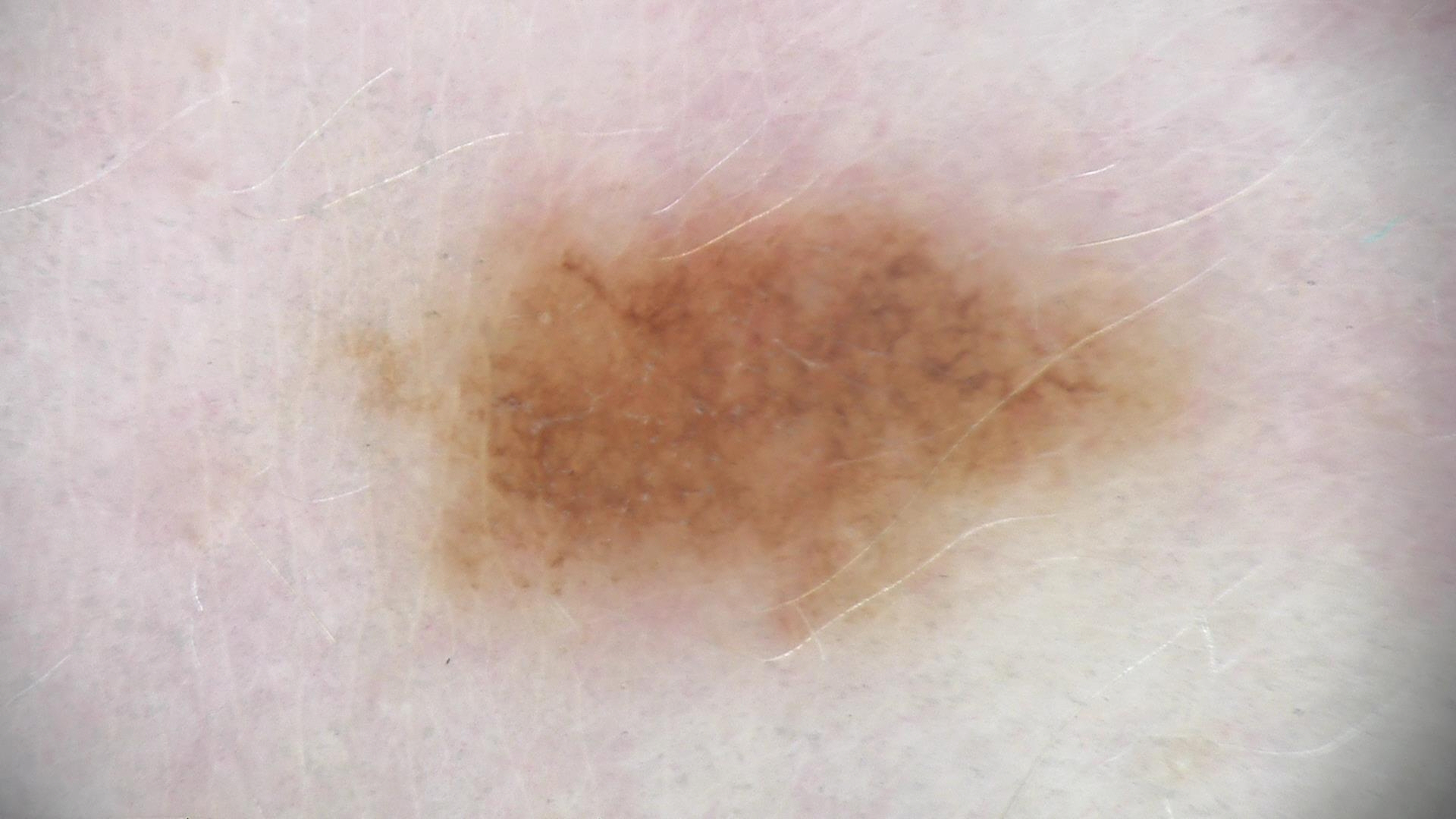image — dermatoscopy; diagnostic label — dysplastic junctional nevus (expert consensus).